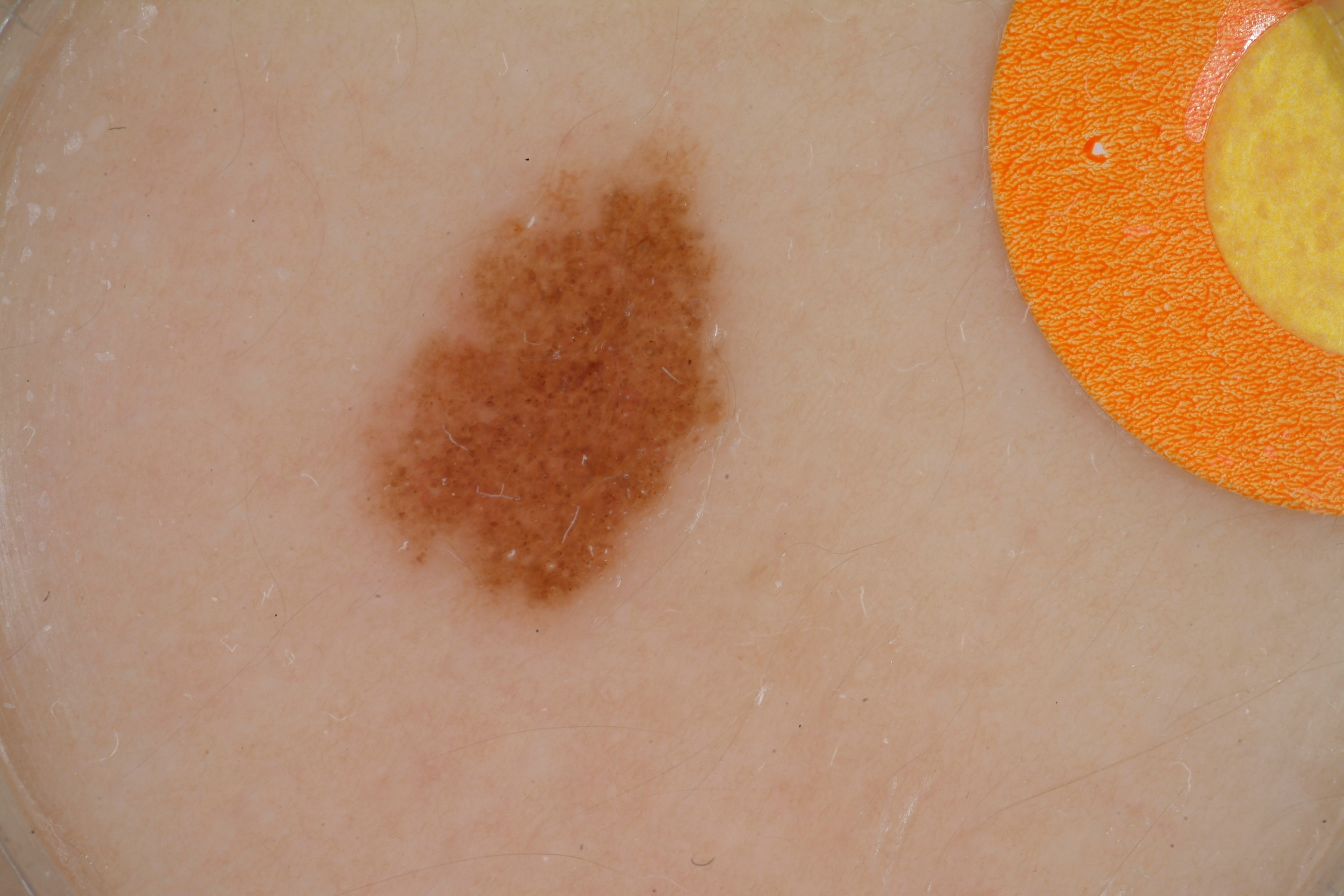Q: What kind of image is this?
A: dermoscopy
Q: Patient demographics?
A: female, about 15 years old
Q: Which dermoscopic features were noted?
A: milia-like cysts and globules; absent: streaks, pigment network, and negative network
Q: Where is the lesion located?
A: (326, 125, 741, 644)
Q: What is this lesion?
A: a melanocytic nevus